A skin lesion imaged with a dermatoscope.
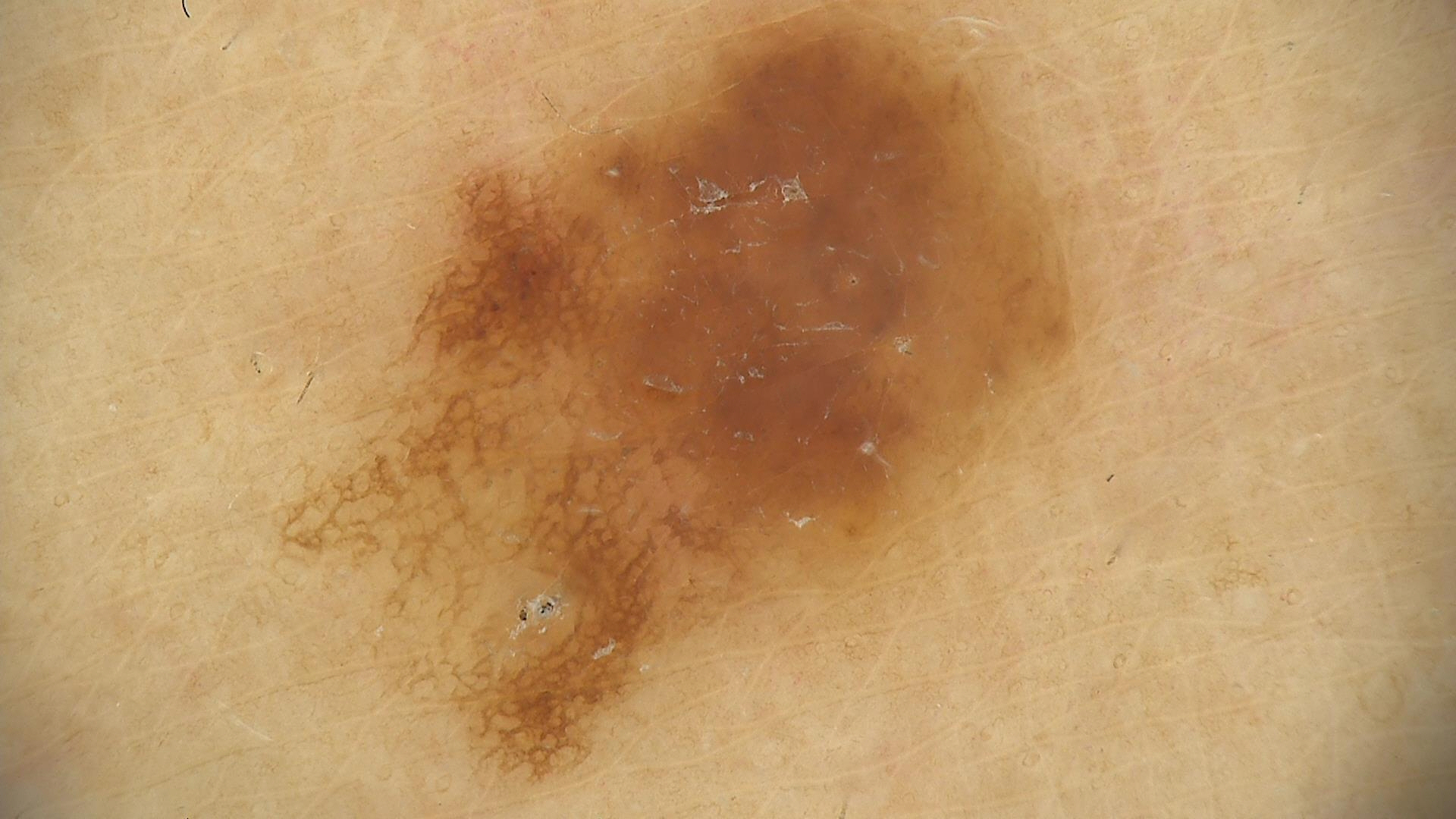The diagnosis was a benign lesion — a dysplastic compound nevus.